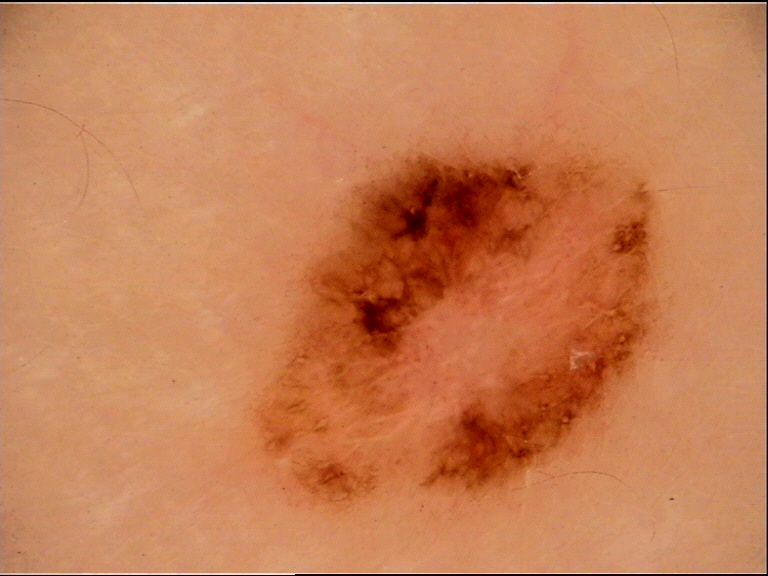image type = dermatoscopy | class = melanoma (biopsy-proven).